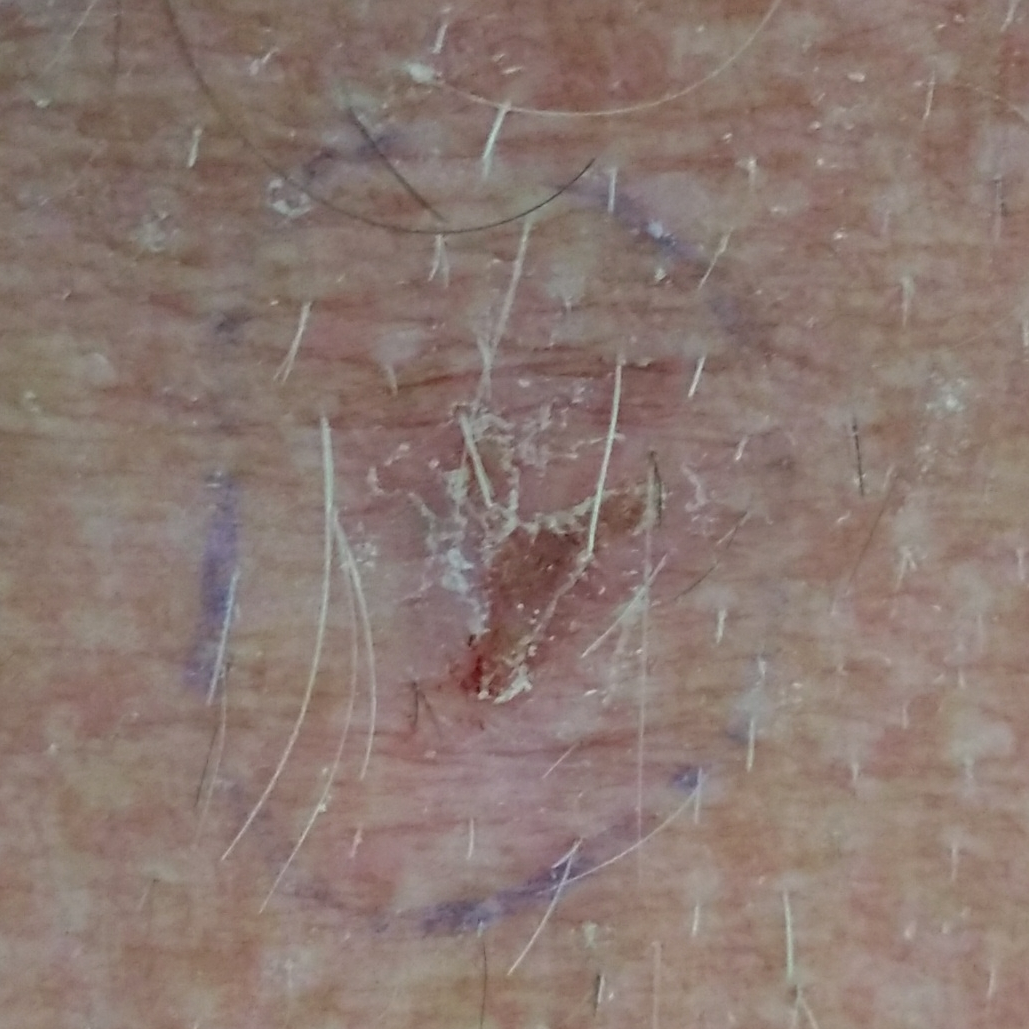Clinical context:
A male subject 47 years old. The chart records prior malignancy (patient or family), alcohol use, pesticide exposure, and no tobacco use. A clinical photograph of a skin lesion. The patient is Fitzpatrick II. The lesion is located on the chest. The patient reports that the lesion has bled, hurts, and itches.
Conclusion:
Histopathological examination showed a skin cancer — a basal cell carcinoma.